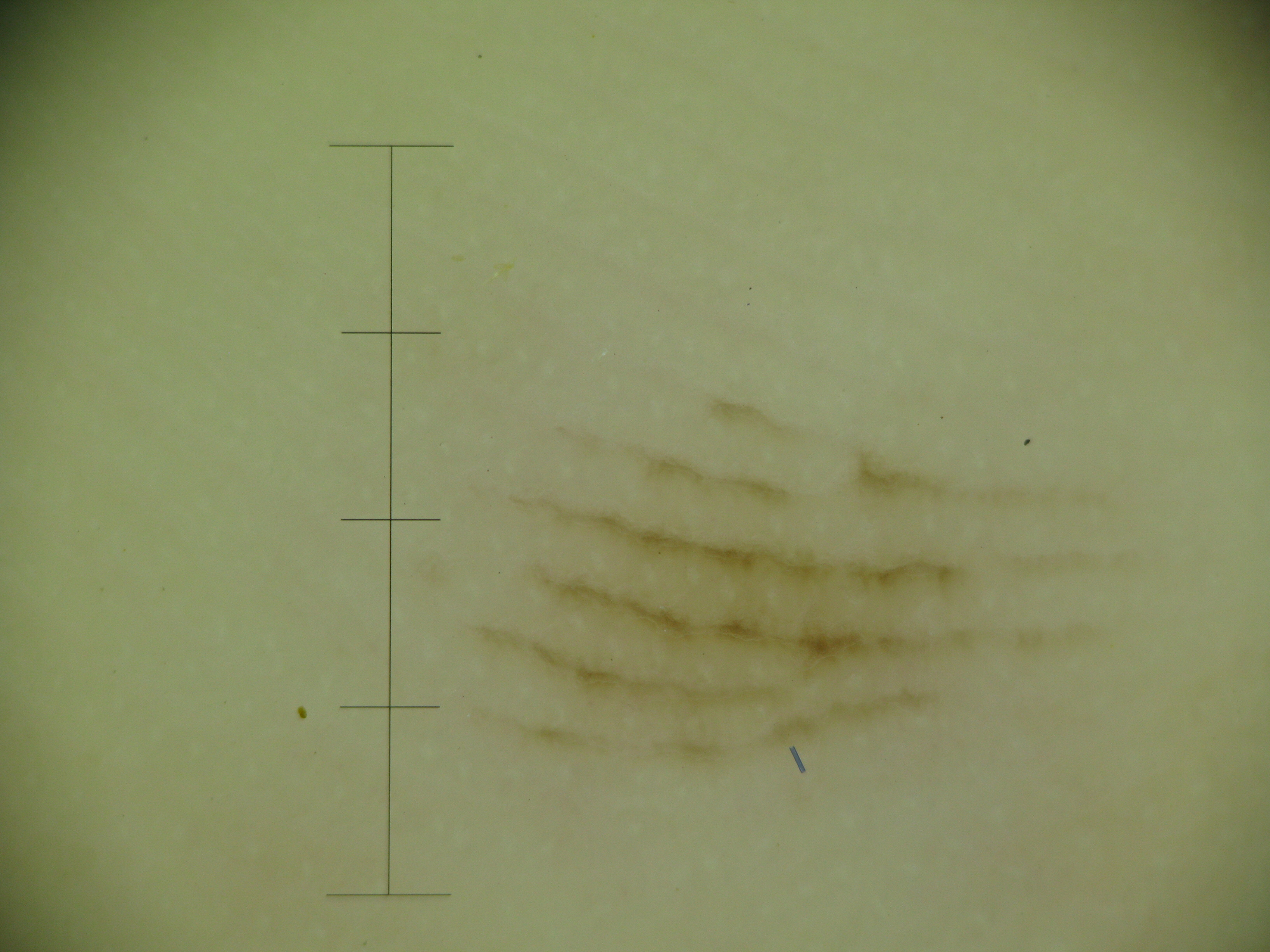| feature | finding |
|---|---|
| imaging | dermatoscopy |
| lesion type | banal |
| diagnostic label | acral junctional nevus (expert consensus) |